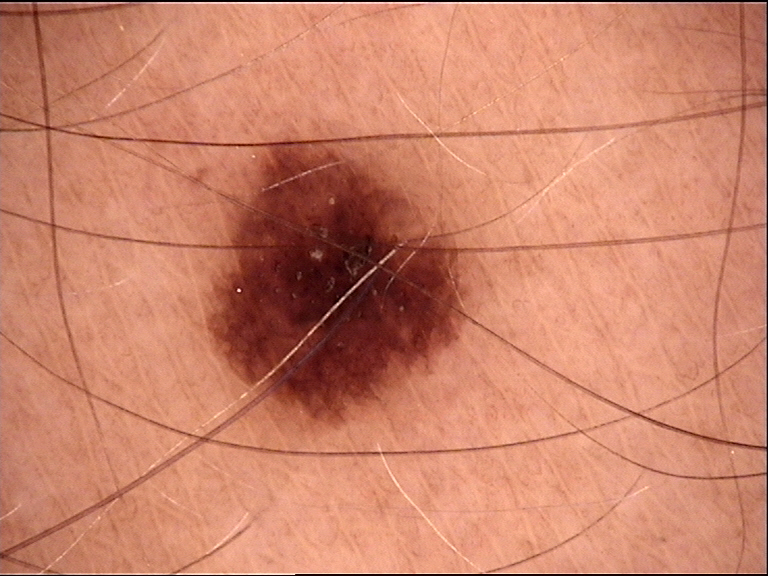Case: A dermoscopic photograph of a skin lesion. Impression: Diagnosed as a dysplastic junctional nevus.